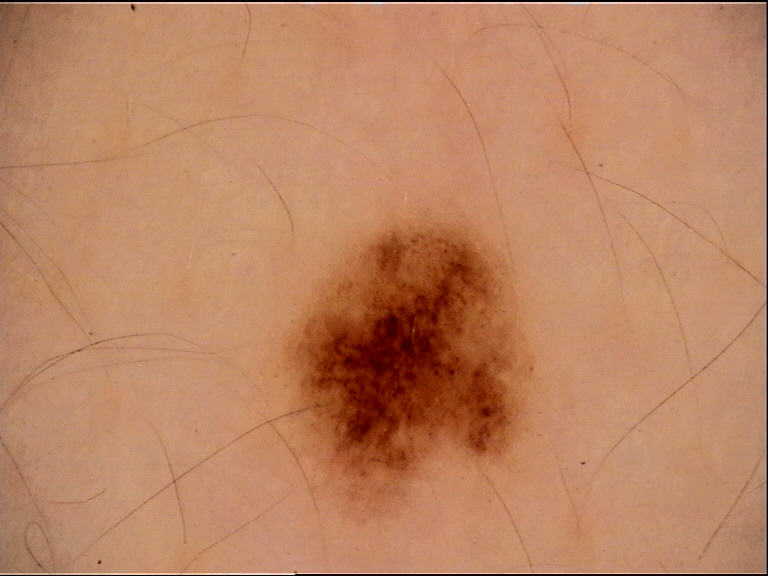Consistent with a benign lesion — a dysplastic junctional nevus.